A clinical photo of a skin lesion taken with a smartphone: 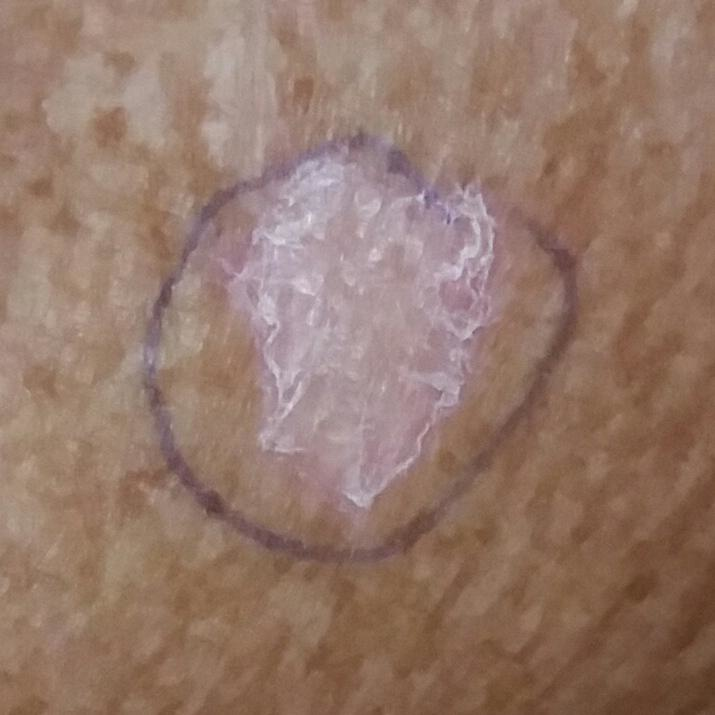The lesion is on the nose. The patient describes that the lesion itches and has grown, but is not elevated. Biopsy-confirmed as a basal cell carcinoma.